A dermoscopic image of a skin lesion.
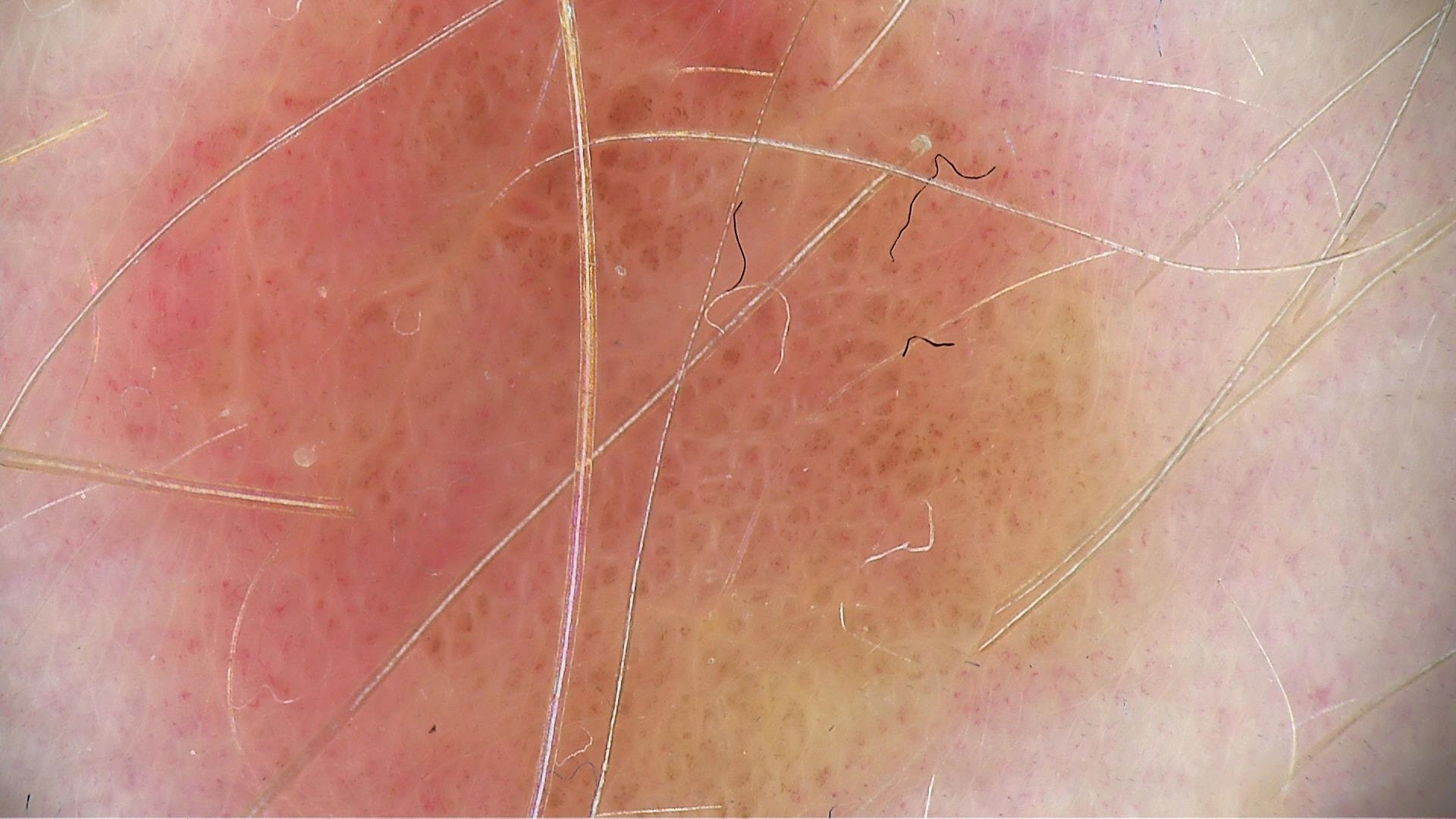This is a banal lesion.
Classified as a compound nevus.